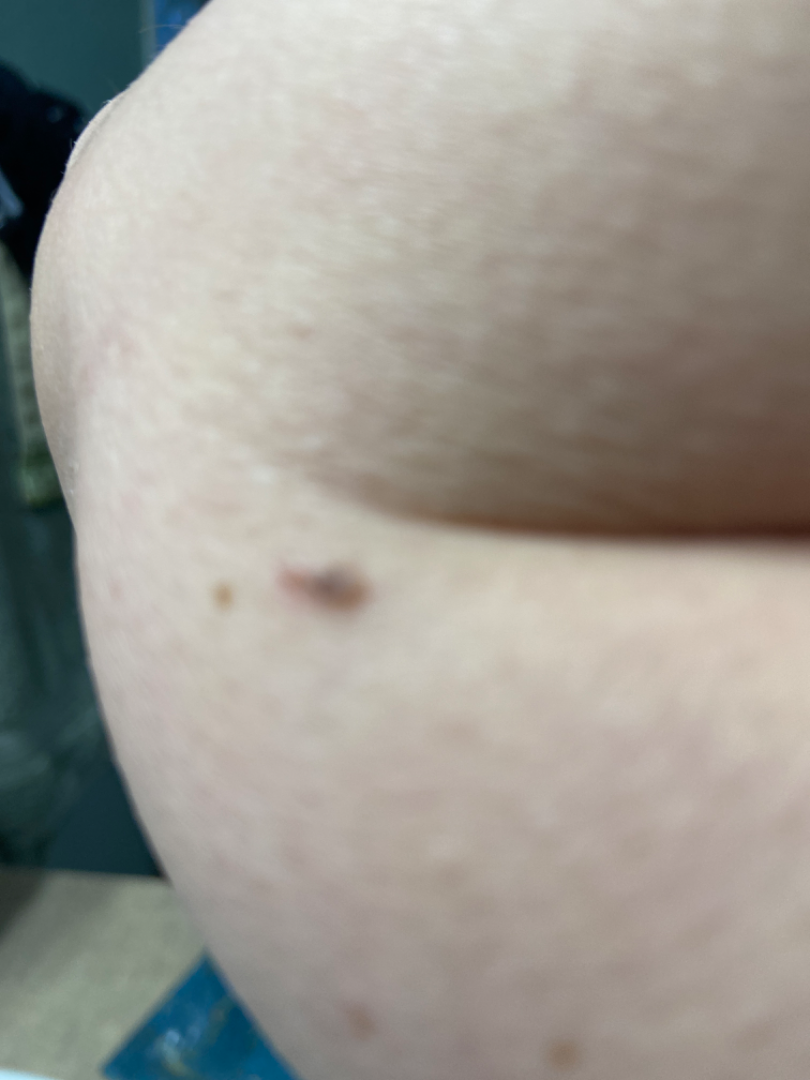Review: The case was indeterminate on photographic review. Patient information: Reported lesion symptoms include darkening, bothersome appearance and itching. FST III. The photograph was taken at an angle. The patient reported no systemic symptoms. The subject is 50–59, female. Located on the arm. Reported duration is three to twelve months. Self-categorized by the patient as a growth or mole.